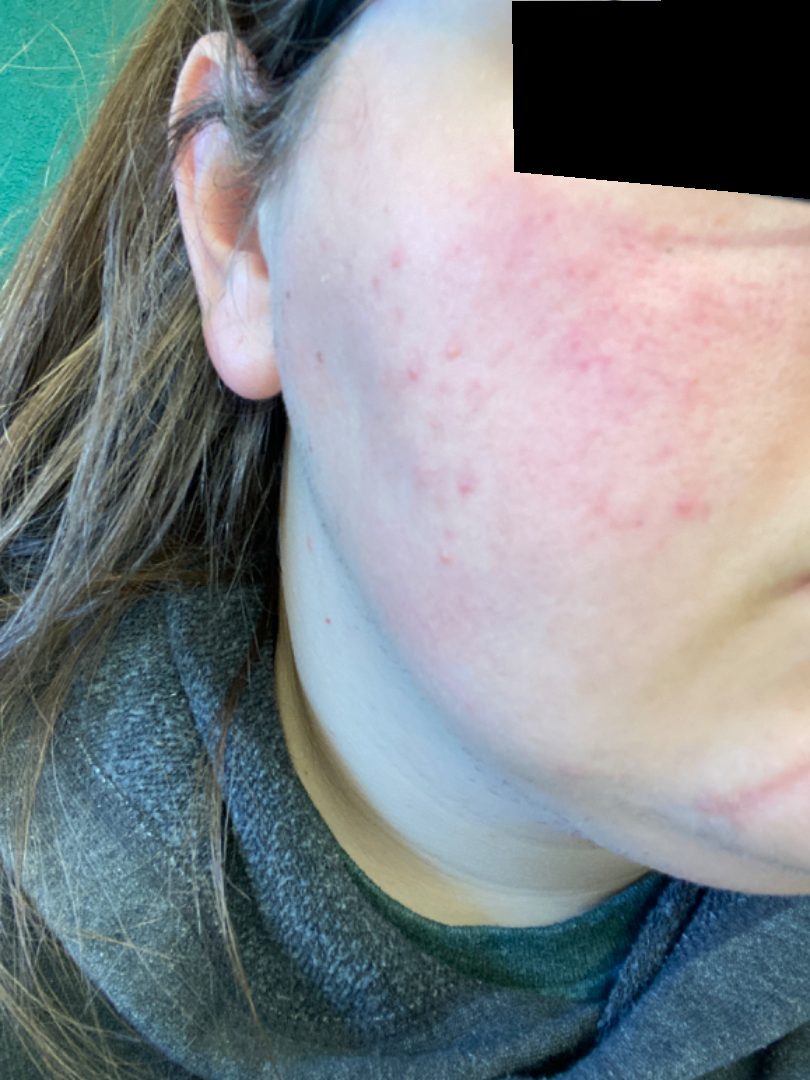other reported symptoms — none reported | image framing — close-up | subject — female, age 18–29 | self-categorized as — a rash | patient-reported symptoms — none reported | skin tone — Fitzpatrick phototype I | differential — consistent with Rosacea.